This is a dermoscopic photograph of a skin lesion.
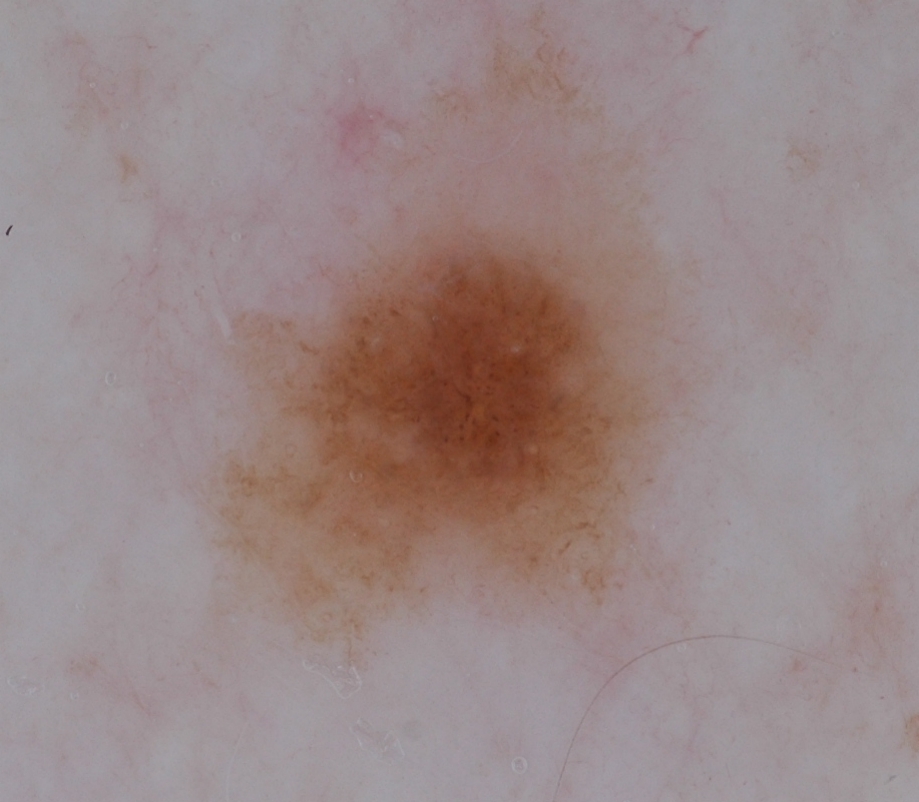Summary:
Dermoscopically, the lesion shows globules; no milia-like cysts, streaks, pigment network, or negative network. In (x1, y1, x2, y2) order, the lesion's extent is bbox(204, 0, 693, 658).
Impression:
Clinically diagnosed as a melanocytic nevus, a benign lesion.